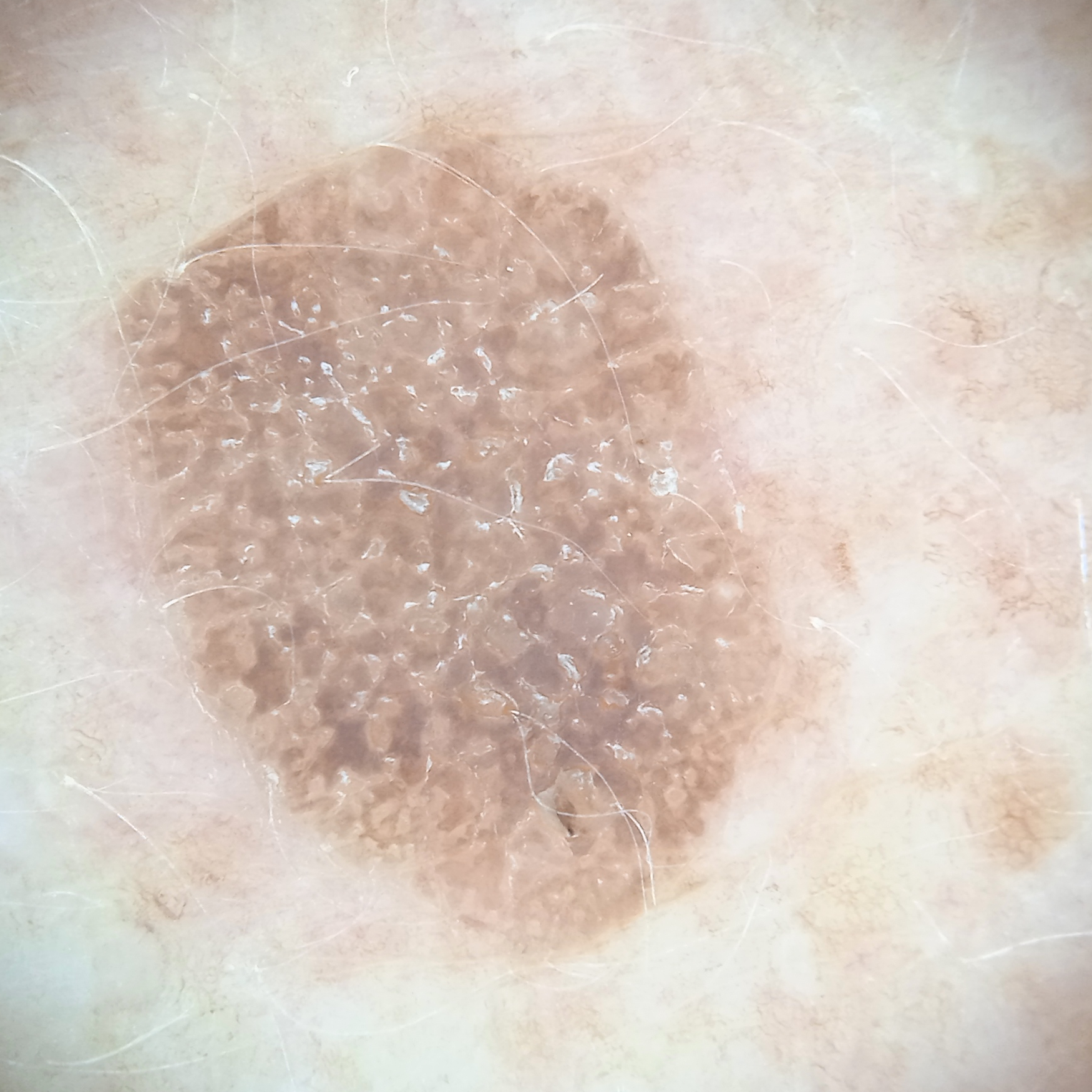modality = dermoscopic image | patient = female, aged 78 | referral context = research study (no referral diagnosis) | size = 9.6 mm | diagnostic label = seborrheic keratosis (dermatologist consensus).